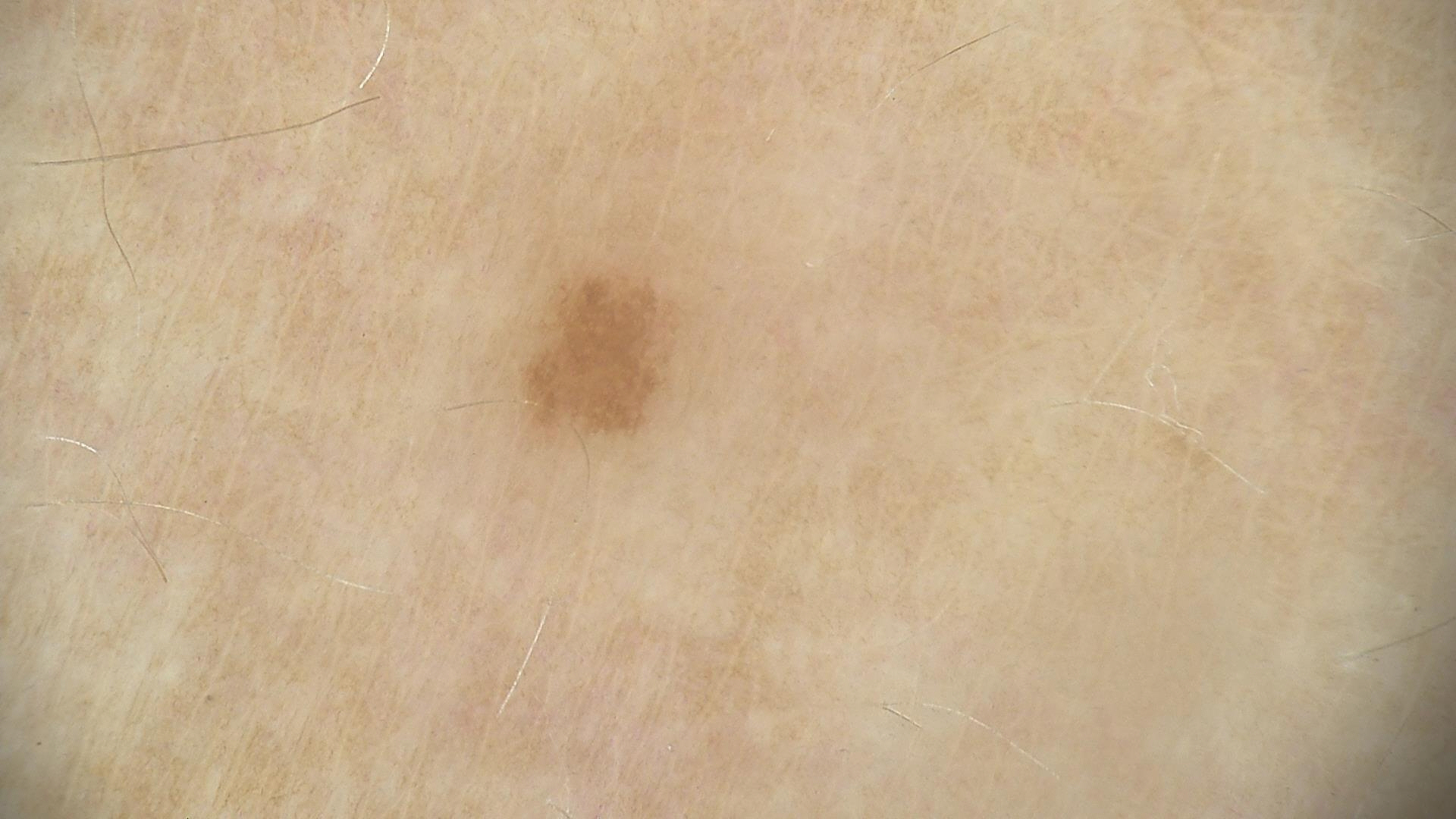| field | value |
|---|---|
| modality | dermatoscopy |
| diagnosis | solar lentigo (expert consensus) |